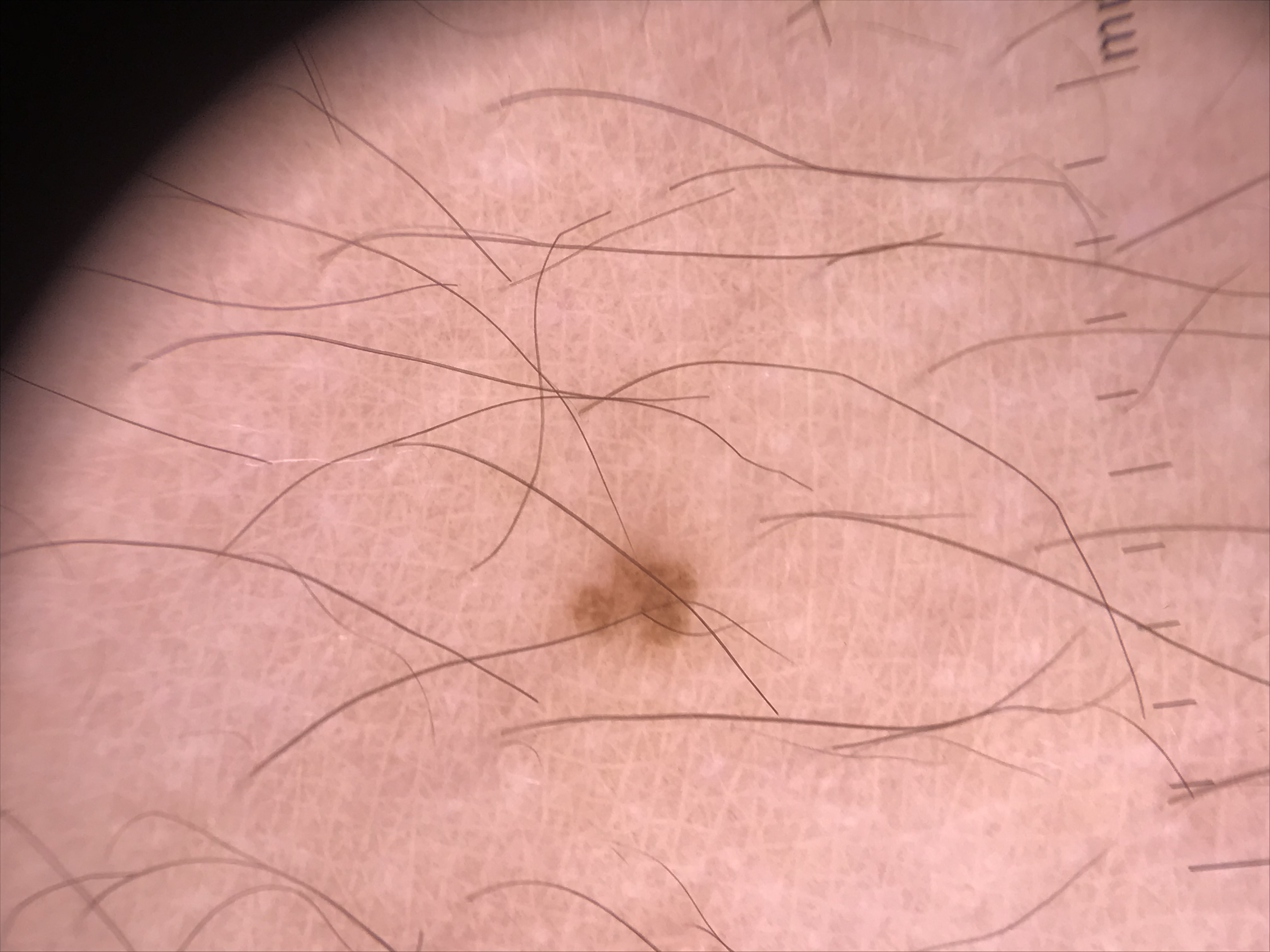Dermoscopy of a skin lesion. The diagnostic label was a banal lesion — a junctional nevus.